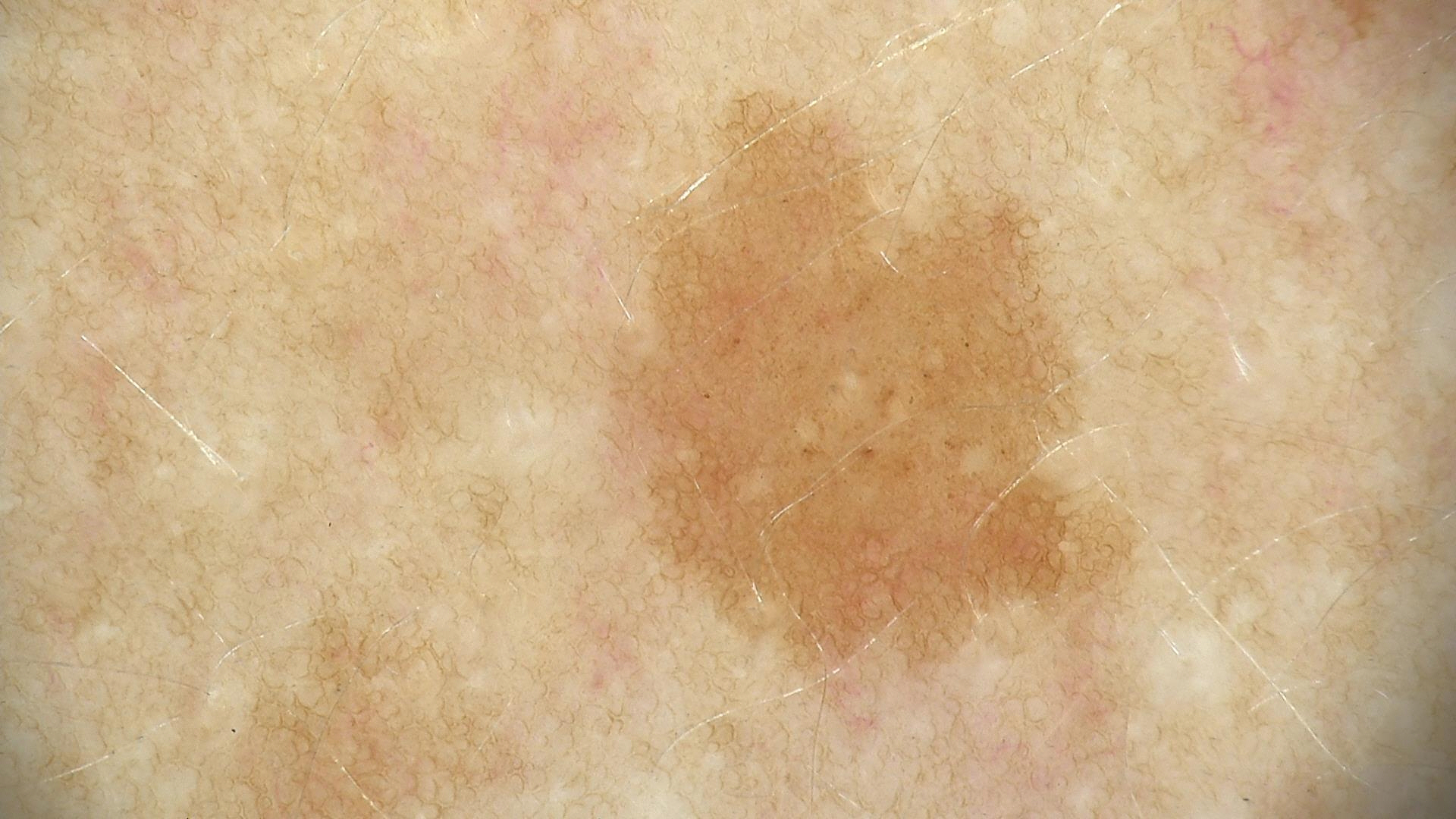A skin lesion imaged with a dermatoscope. The diagnosis was a benign lesion — a dysplastic junctional nevus.